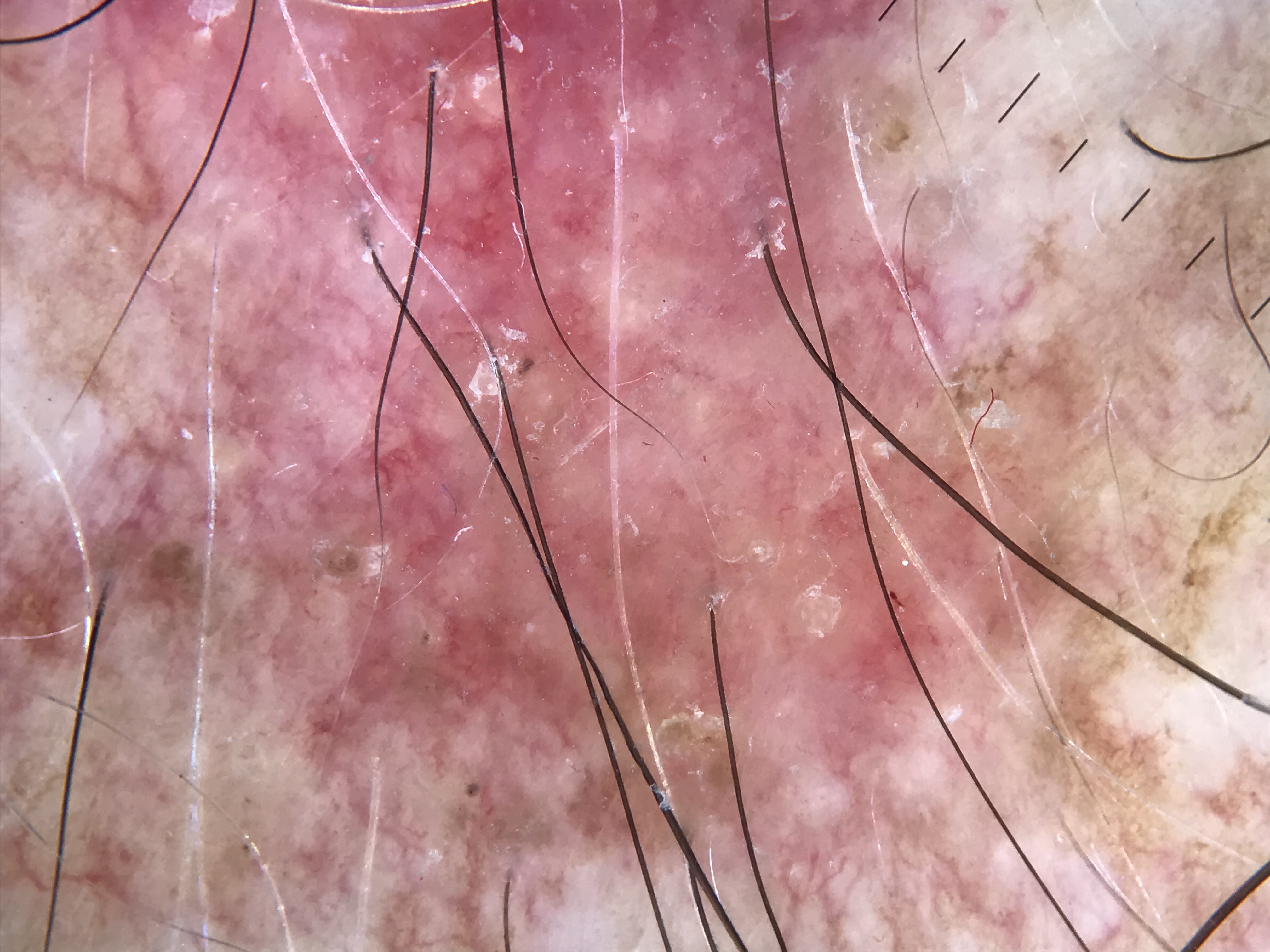Dermoscopy of a skin lesion. The architecture is that of a keratinocytic lesion. Diagnosed as an actinic keratosis.